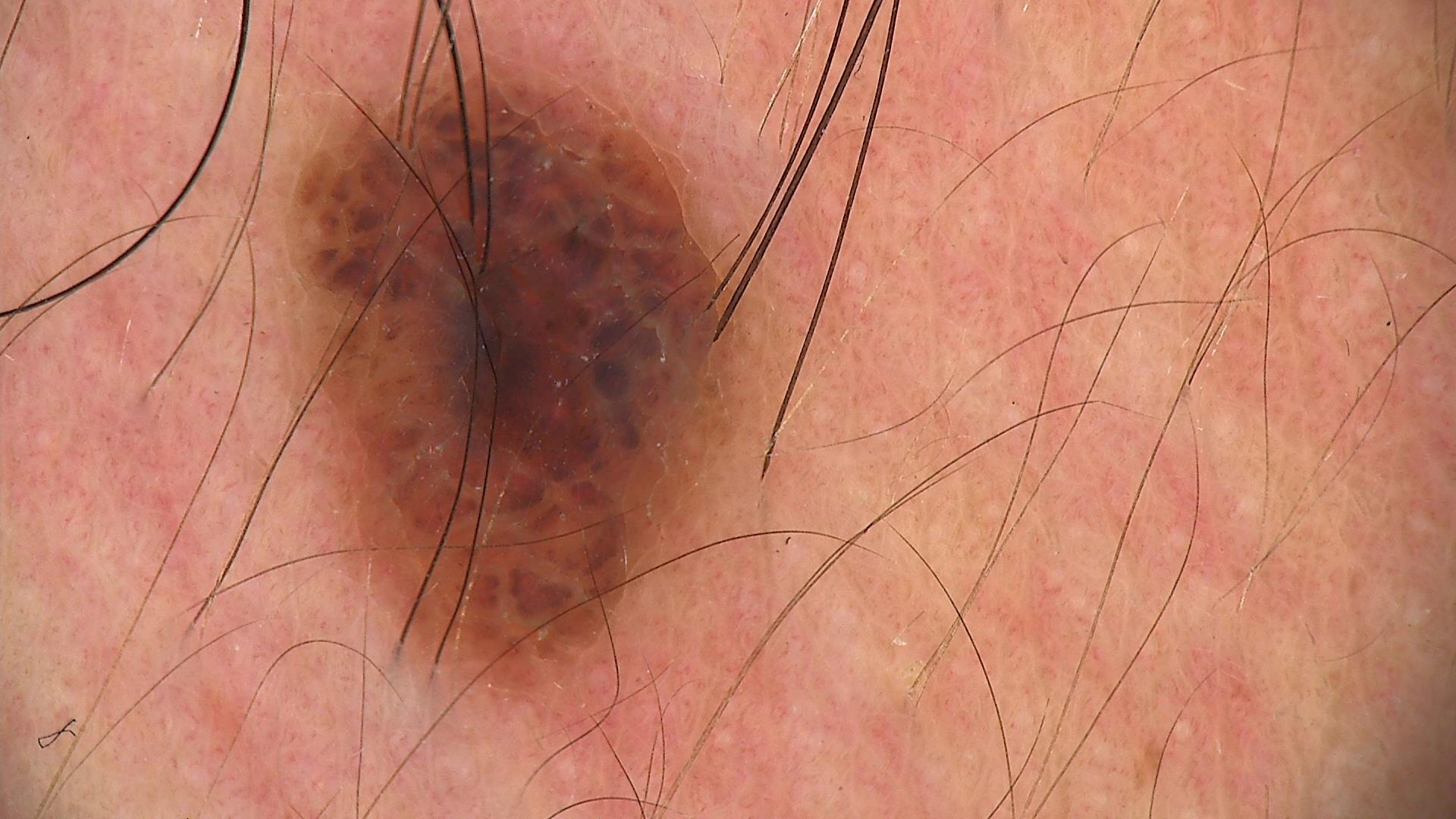Case:
– image type — dermatoscopy
– classification — banal
– assessment — compound nevus (expert consensus)